This image was taken at an angle · located on the top or side of the foot — 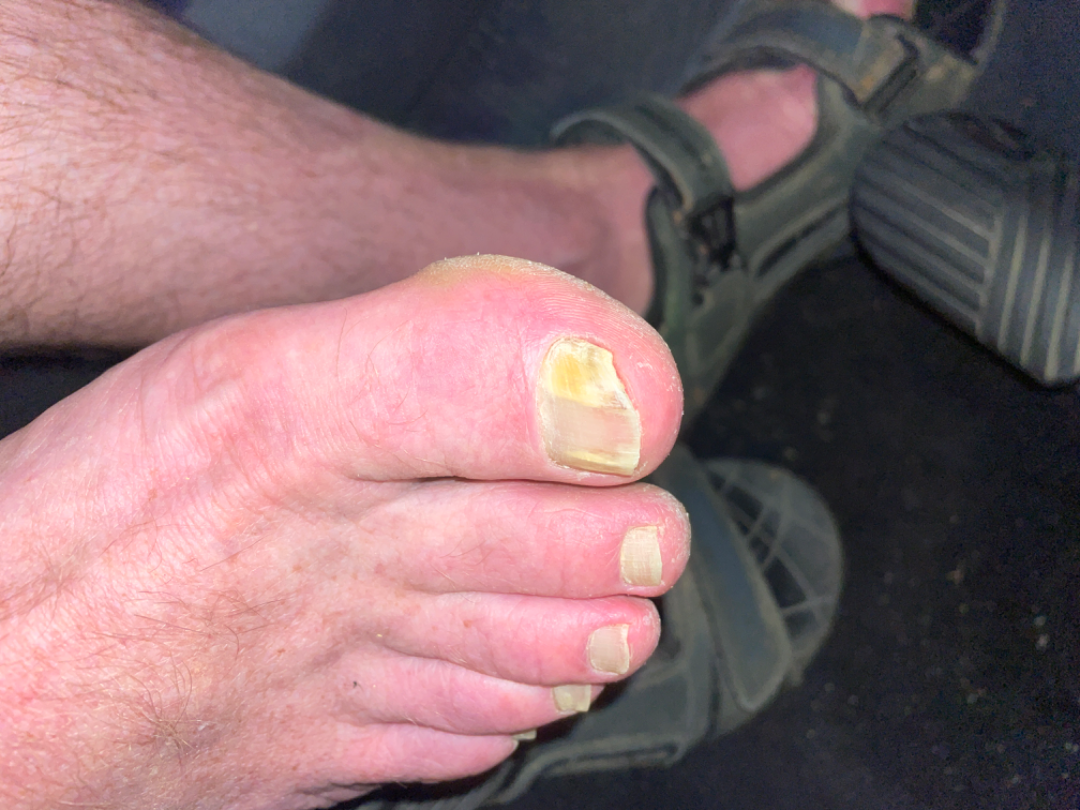Findings:
The leading consideration is Onychomycosis; also consider Psoriasis; possibly Nail dystrophy due to trauma.